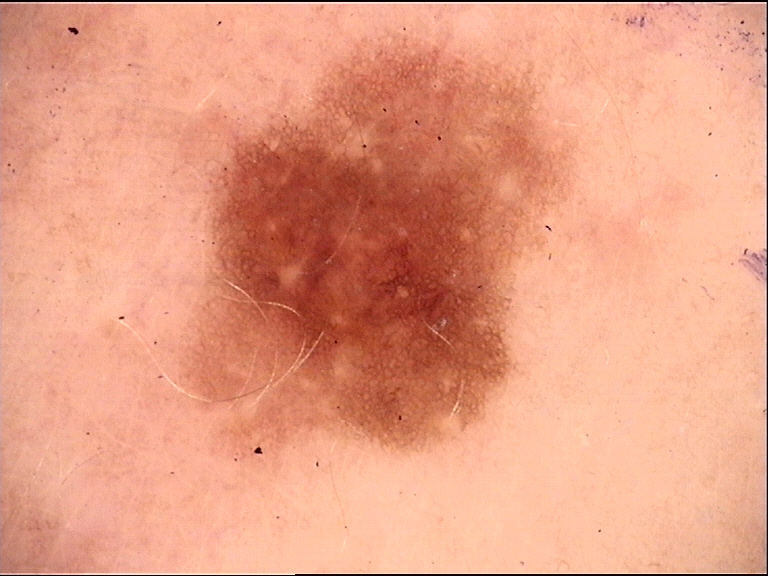modality: dermoscopy
diagnostic label: dysplastic junctional nevus (expert consensus)